An image taken at an angle; the contributor is 30–39, female; located on the arm, back of the hand, leg and top or side of the foot:
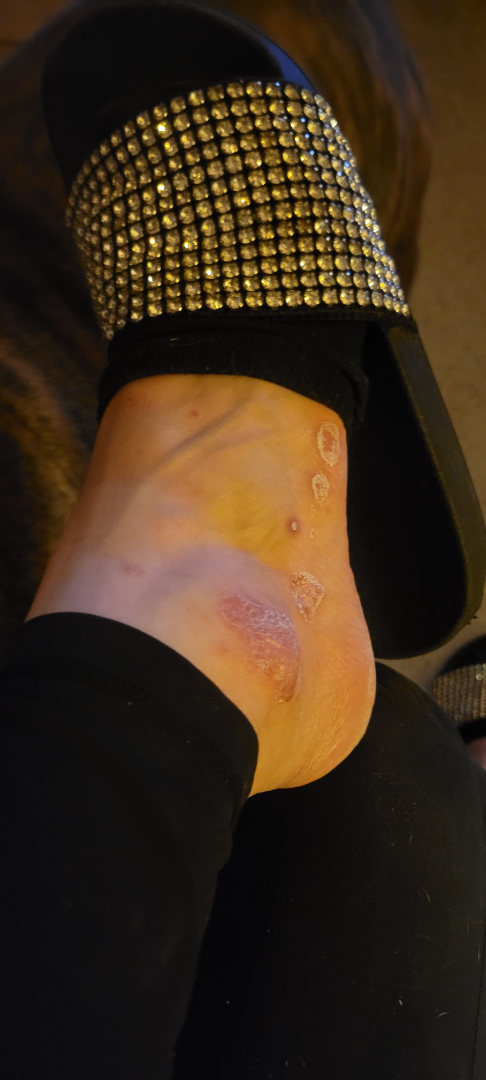Clinical context: The patient also reports fatigue. The patient reports bothersome appearance and itching. The patient reports the condition has been present for one to three months. The patient reports the lesion is rough or flaky and flat. Assessment: The reviewing clinician's impression was: Psoriasis (primary); Tinea (considered); Eczema (considered).